The contributor notes itching and bothersome appearance. Reported duration is less than one week. Self-categorized by the patient as acne. Located on the back of the hand and arm. Male contributor, age 18–29. An image taken at a distance:
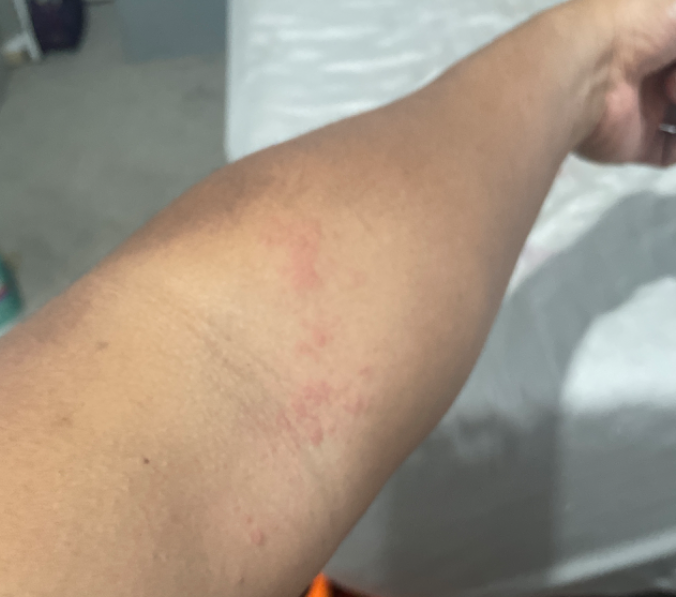On teledermatology review, Eczema (primary); Allergic Contact Dermatitis (possible).